Symptoms reported: bothersome appearance; the affected area is the arm; the patient notes the lesion is flat; the condition has been present for one to three months; a close-up photograph:
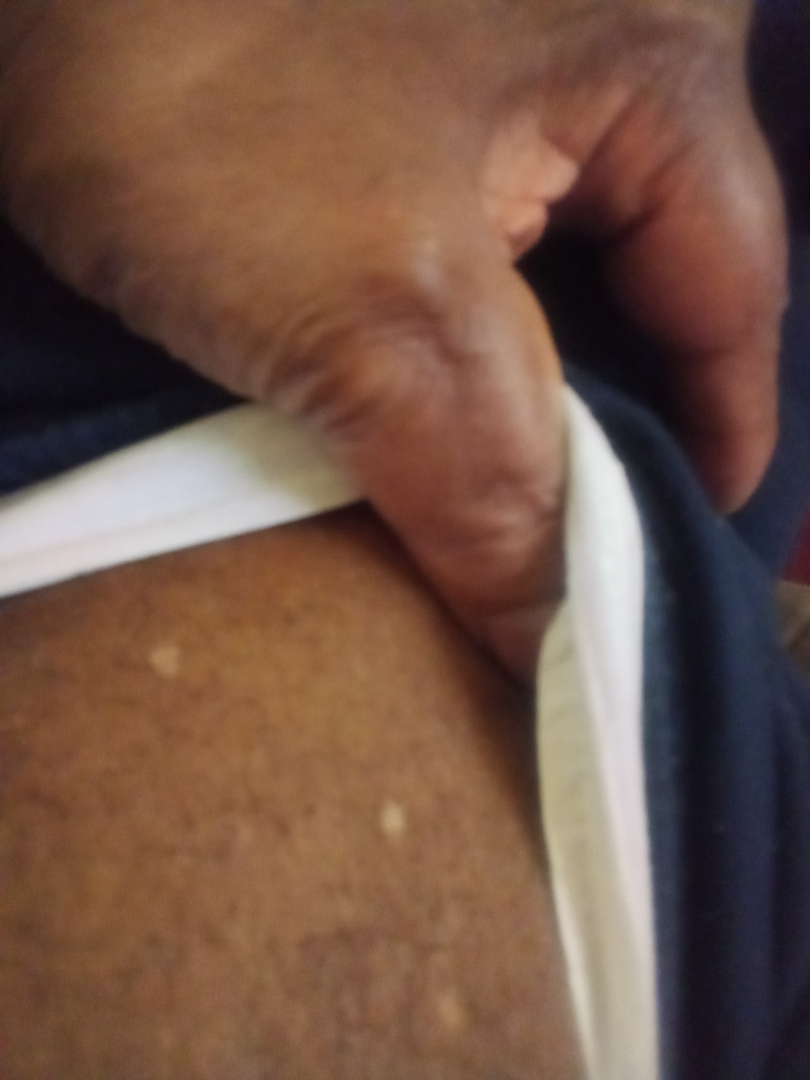Findings: The dermatologist could not determine a likely condition from the photograph alone.